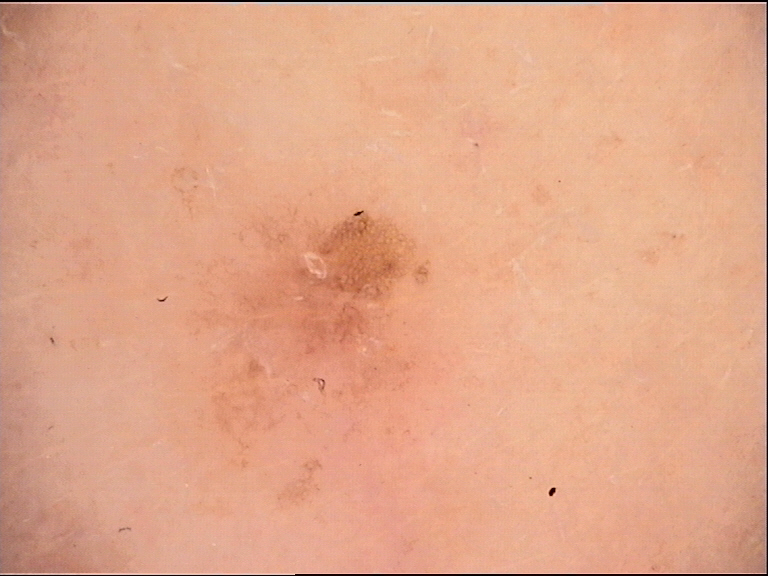A skin lesion imaged with a dermatoscope. This is a banal lesion. Diagnosed as a junctional nevus.